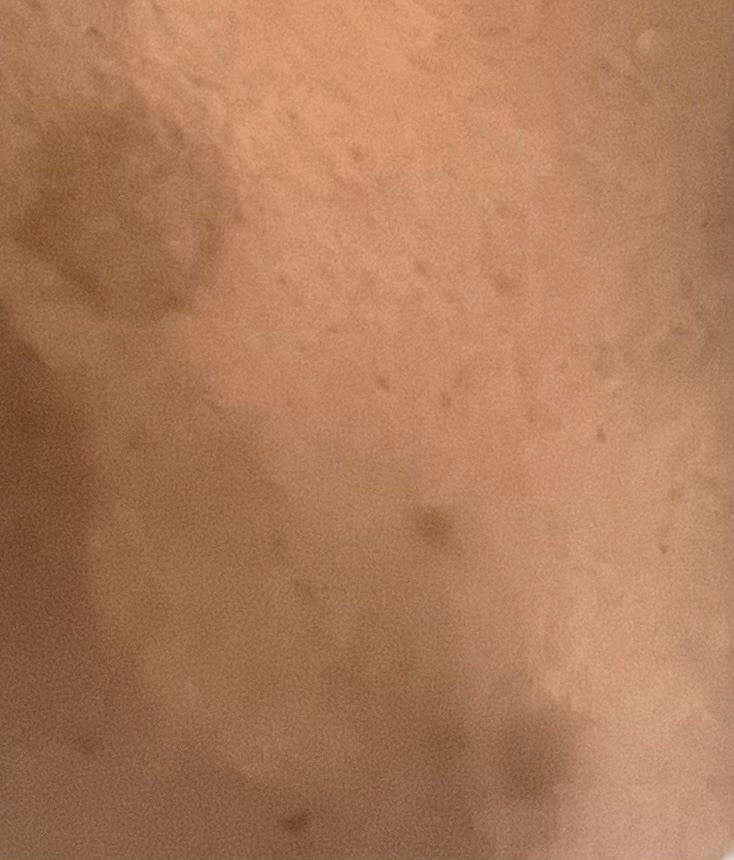Review:
The image was not sufficient for the reviewer to characterize the skin condition.